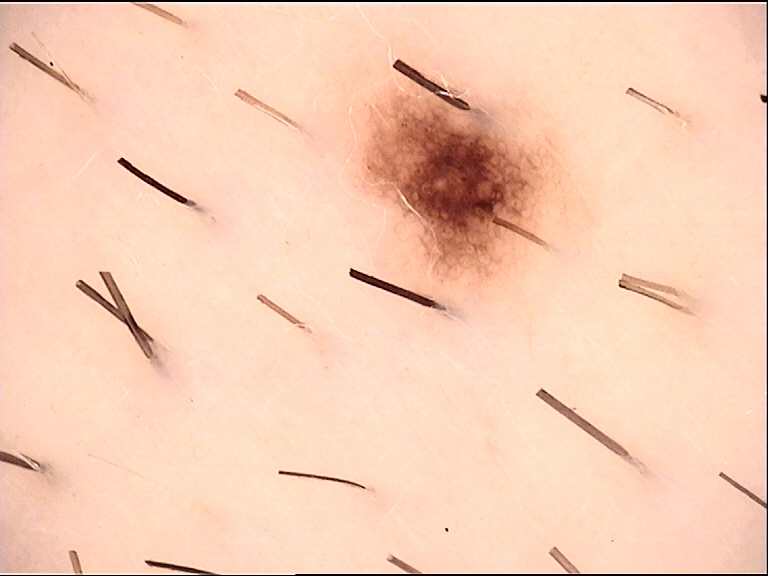Classified as a benign lesion — a dysplastic junctional nevus.